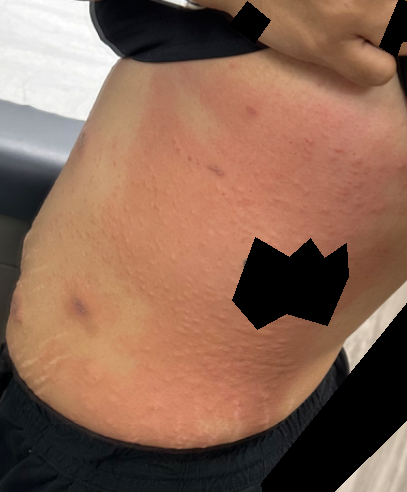  differential:
    leading:
      - Hypersensitivity
    considered:
      - Drug Rash
      - Viral Exanthem
    unlikely:
      - Allergic Contact Dermatitis